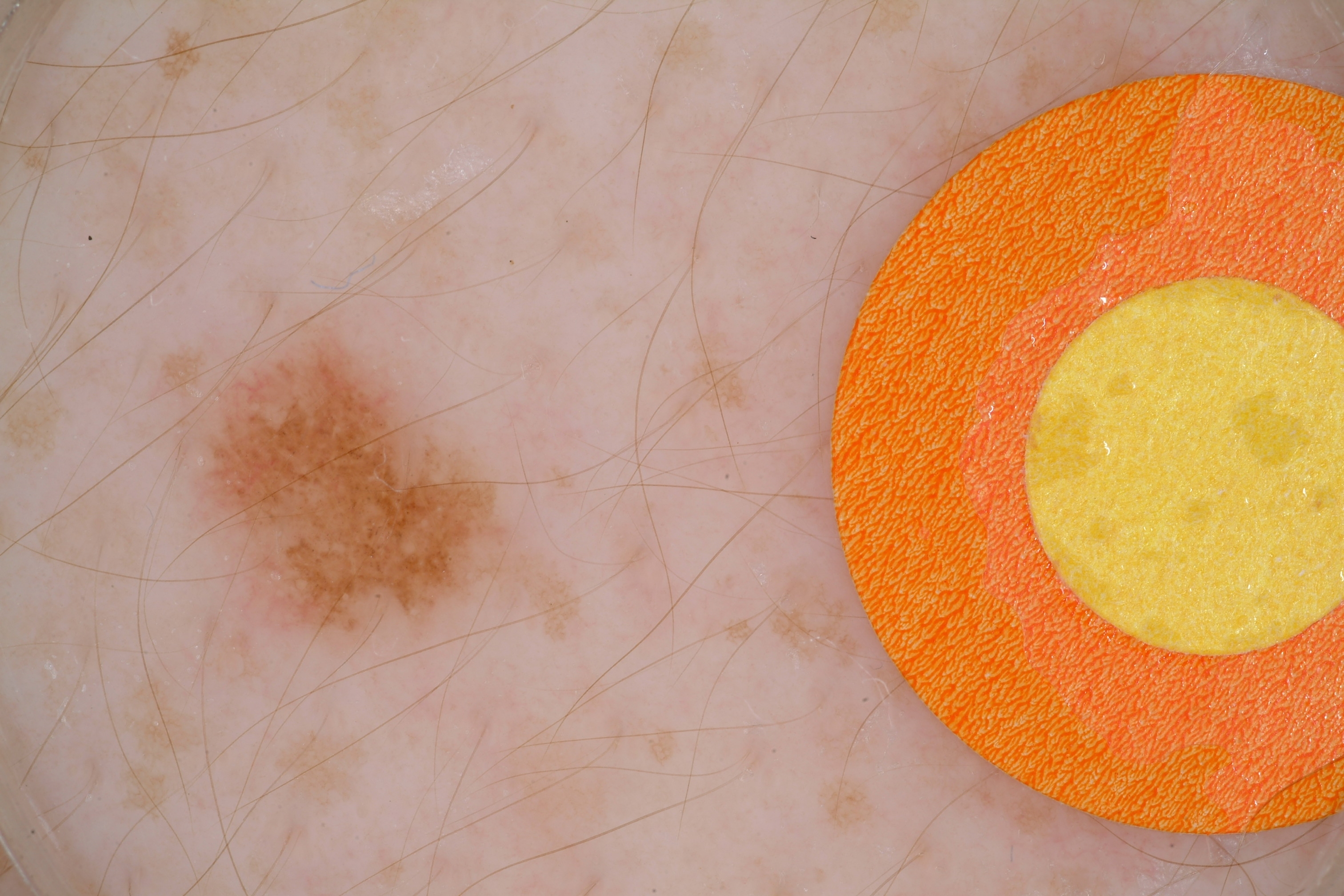{
  "image": {
    "modality": "dermoscopy"
  },
  "dermoscopic_features": {
    "present": [
      "globules"
    ],
    "absent": [
      "pigment network",
      "milia-like cysts",
      "negative network",
      "streaks"
    ]
  },
  "lesion_extent": "small",
  "lesion_location": {
    "bbox_xyxy": [
      169,
      315,
      527,
      649
    ]
  },
  "diagnosis": {
    "name": "melanocytic nevus",
    "malignancy": "benign",
    "lineage": "melanocytic",
    "provenance": "clinical"
  }
}